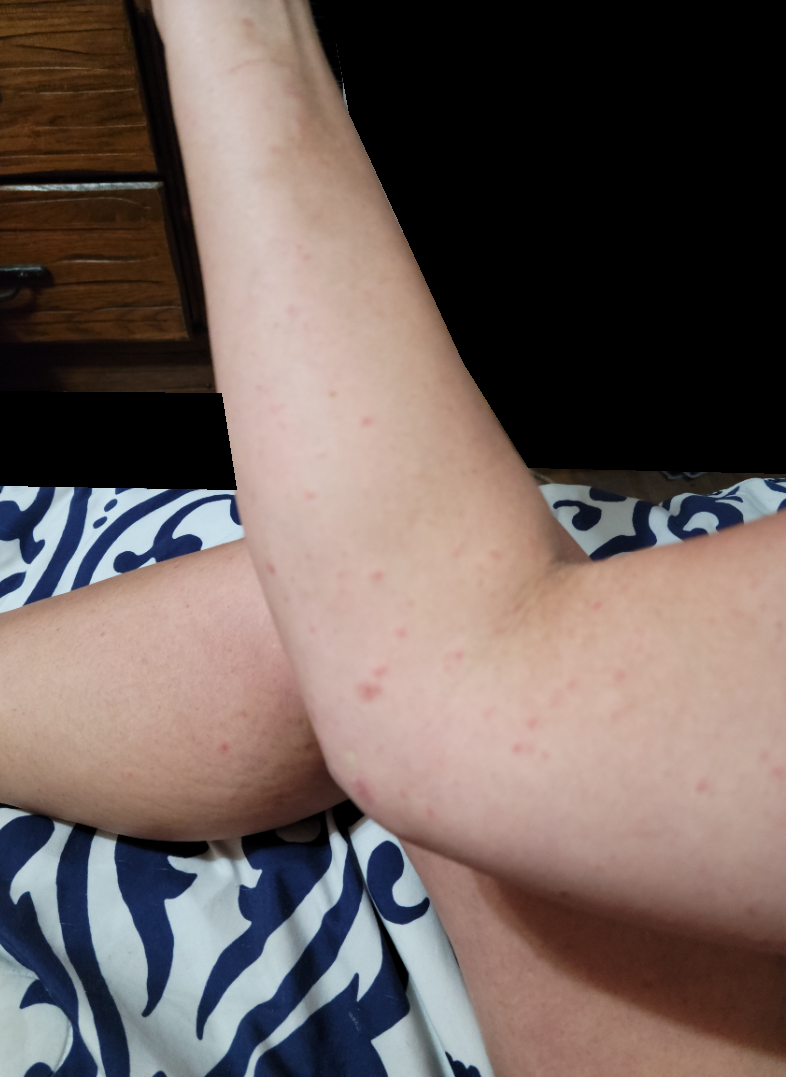The reviewing dermatologists' impression was: most consistent with Psoriasis; an alternative is Lichen planus/lichenoid eruption; less likely is Scabies; less probable is Lymphomatoid papulosis; lower on the differential is Pityriasis lichenoides.